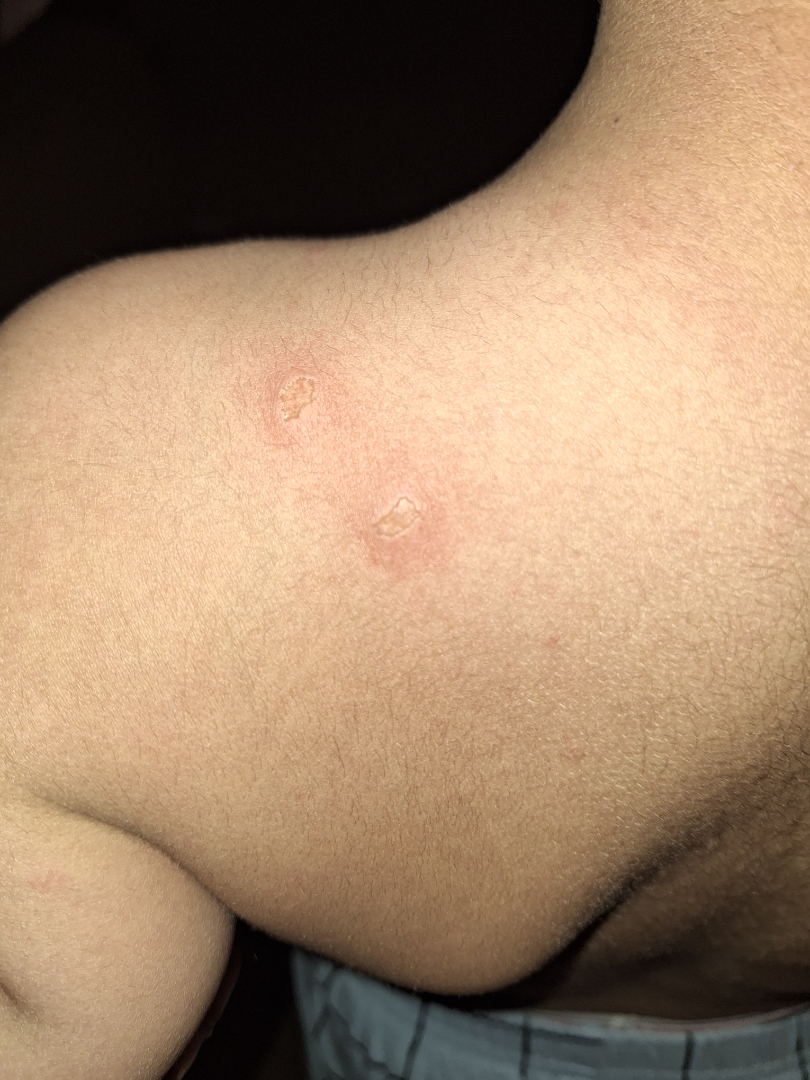No differential diagnosis could be assigned on photographic review.